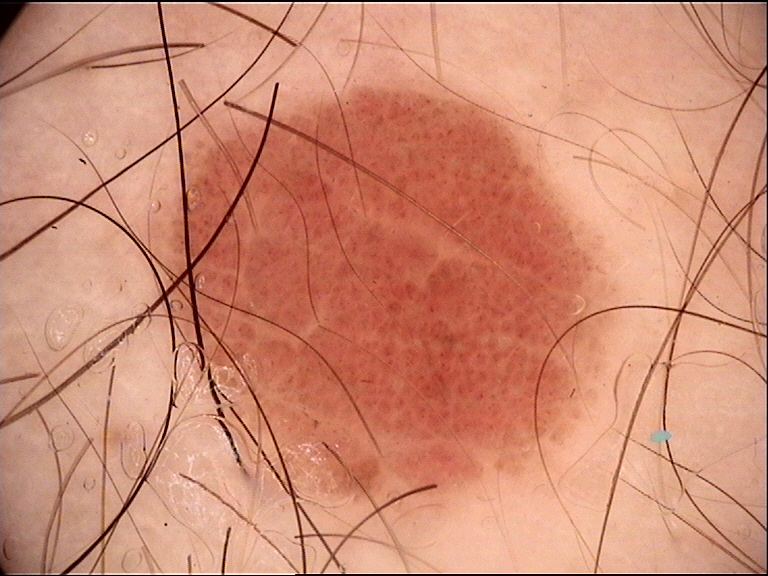Diagnosed as a compound nevus.